Dermoscopy of a skin lesion:
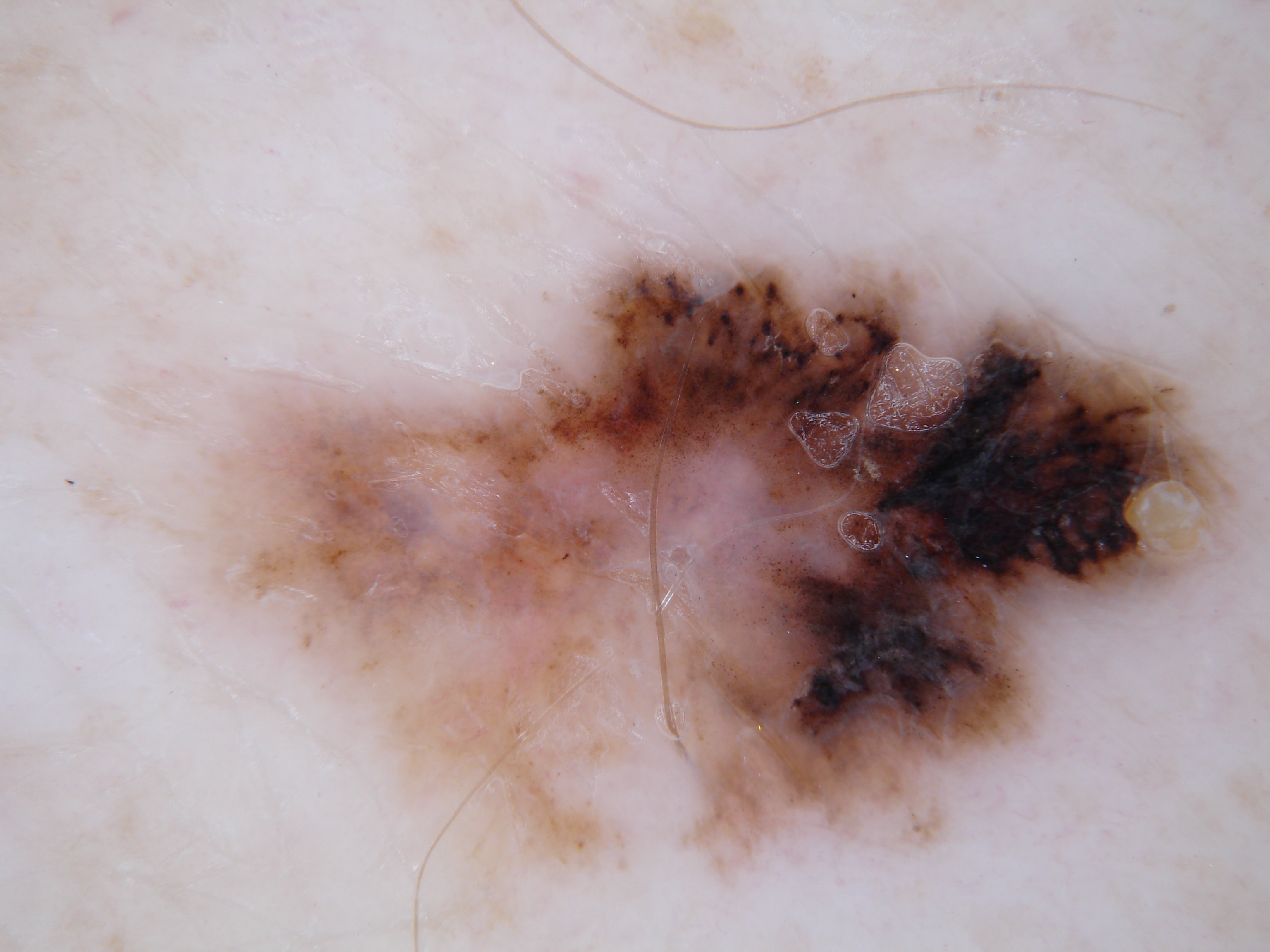{"dermoscopic_features": {"present": ["globules", "streaks"], "absent": ["pigment network", "milia-like cysts", "negative network"]}, "lesion_location": {"bbox_xyxy": [193, 240, 1268, 899]}, "diagnosis": {"name": "melanoma", "malignancy": "malignant", "lineage": "melanocytic", "provenance": "histopathology"}}